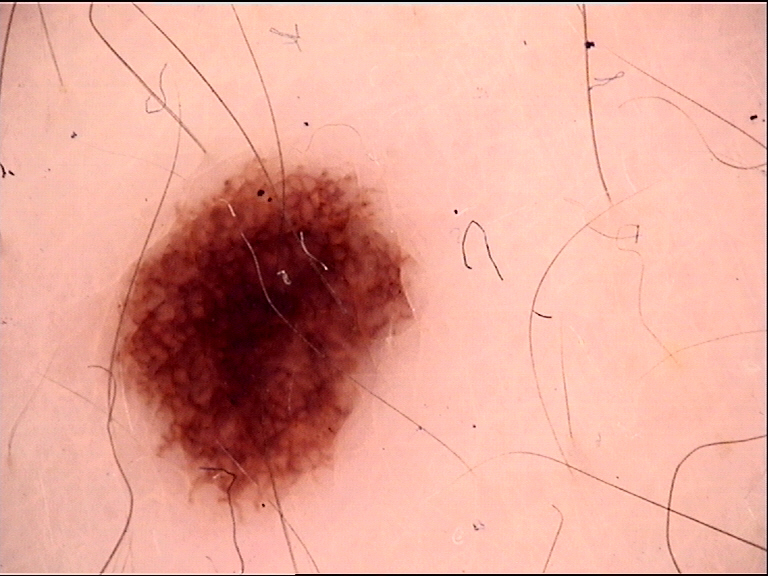Findings: A dermoscopic close-up of a skin lesion. Impression: Diagnosed as a dysplastic junctional nevus.